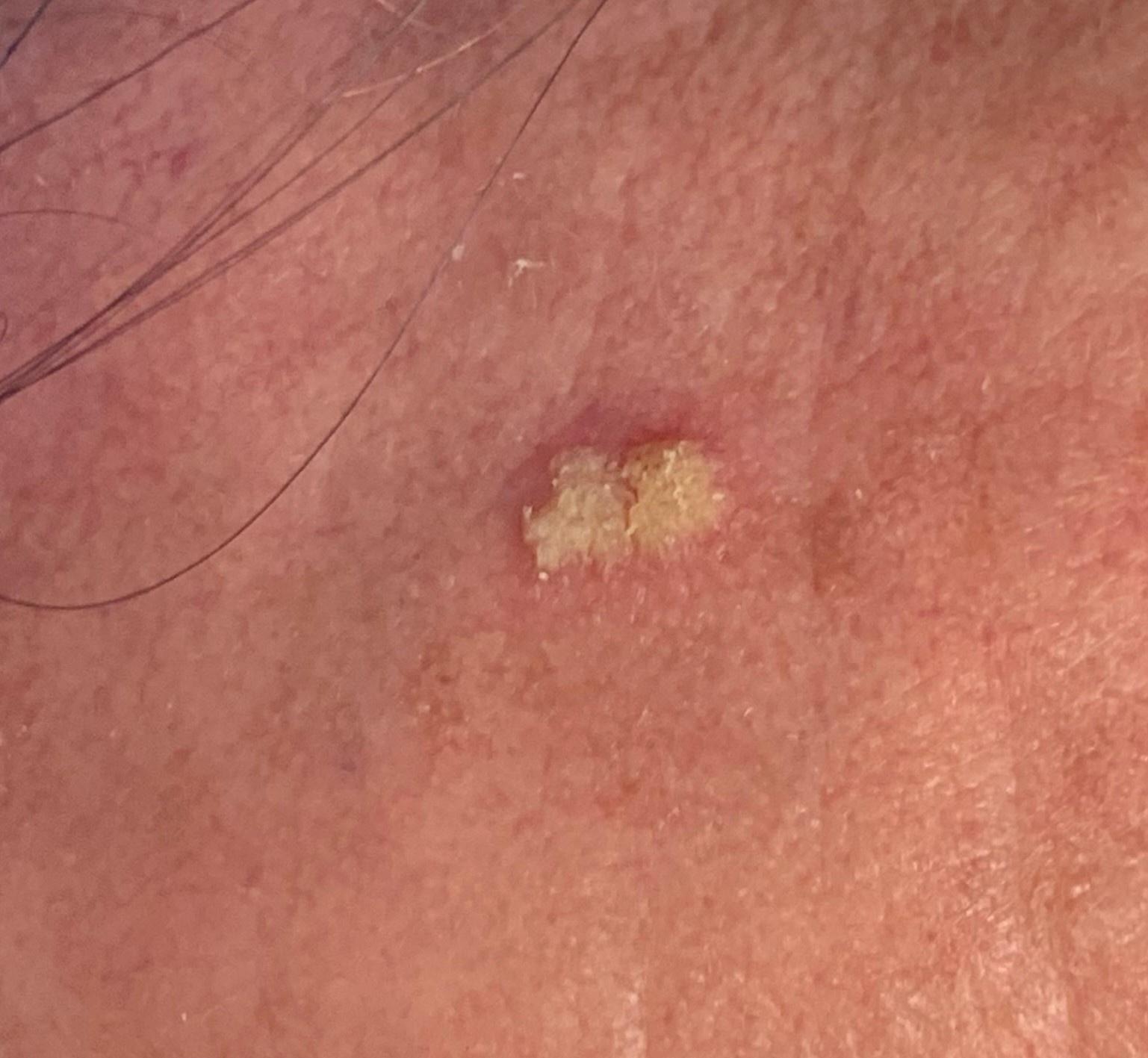Recorded as skin type II. A wide-field clinical photograph of a skin lesion. A male patient aged 68 to 72. The lesion was found on the head or neck. On biopsy, the diagnosis was a malignancy — a squamous cell carcinoma.